Dermoscopy of a skin lesion:
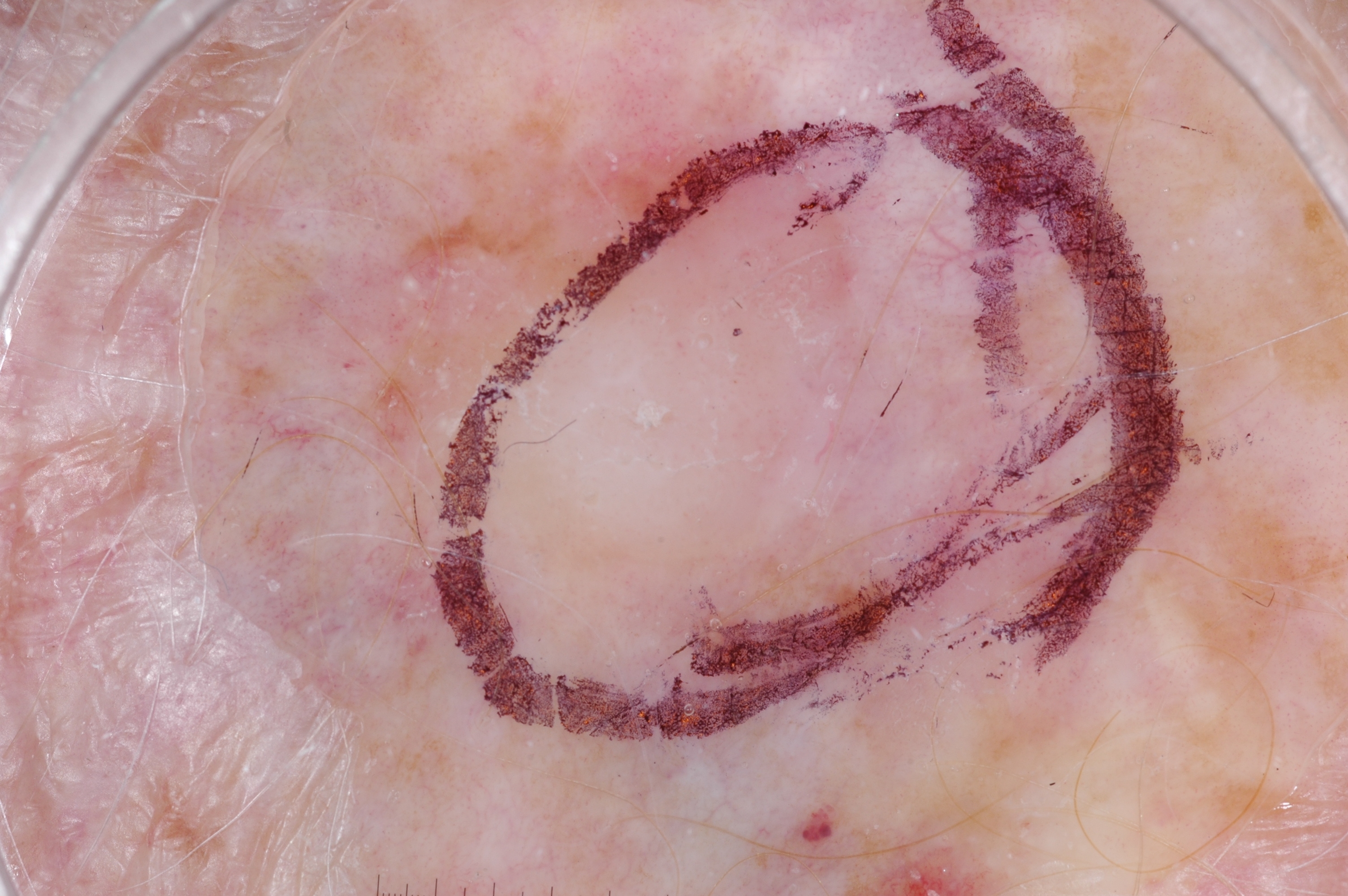lesion bbox: <box>282, 41, 1243, 835</box>; dermoscopic features assessed but absent: pigment network, milia-like cysts, negative network, and streaks; assessment: a seborrheic keratosis, a benign lesion.